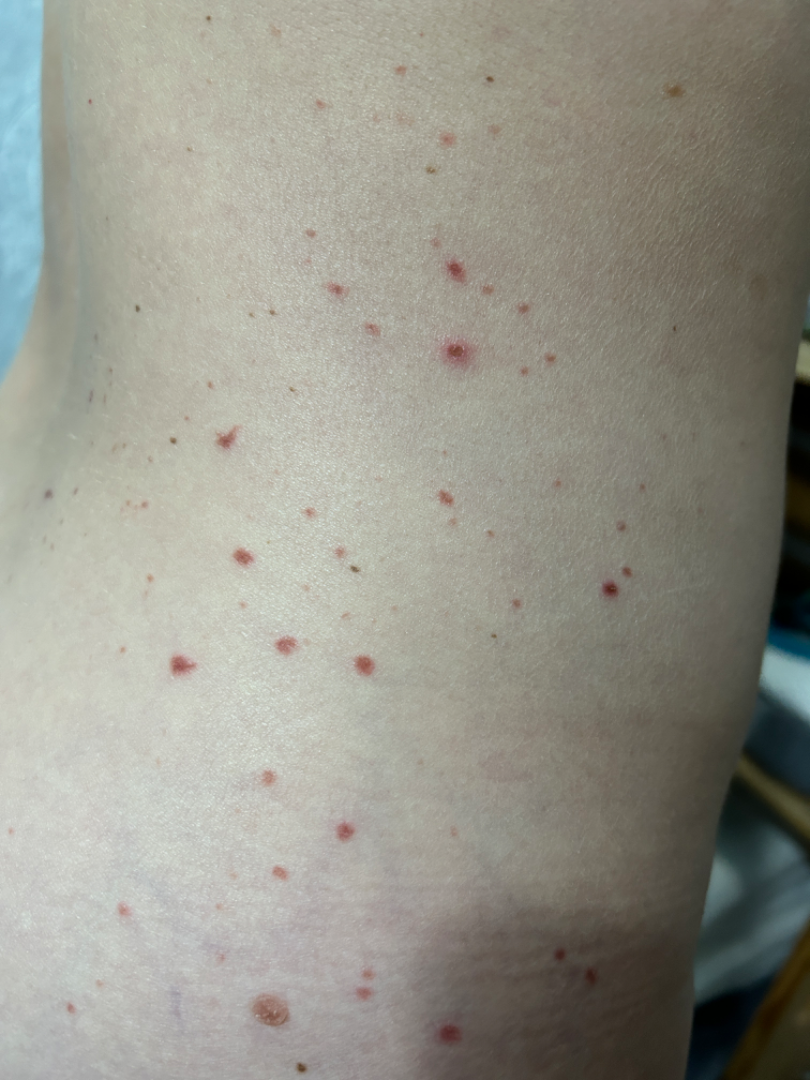Fitzpatrick III.
The photograph is a close-up of the affected area.
One reviewing dermatologist: the differential includes Pityriasis lichenoides and Insect Bite, with no clear leading consideration.